Dermoscopy of a skin lesion: 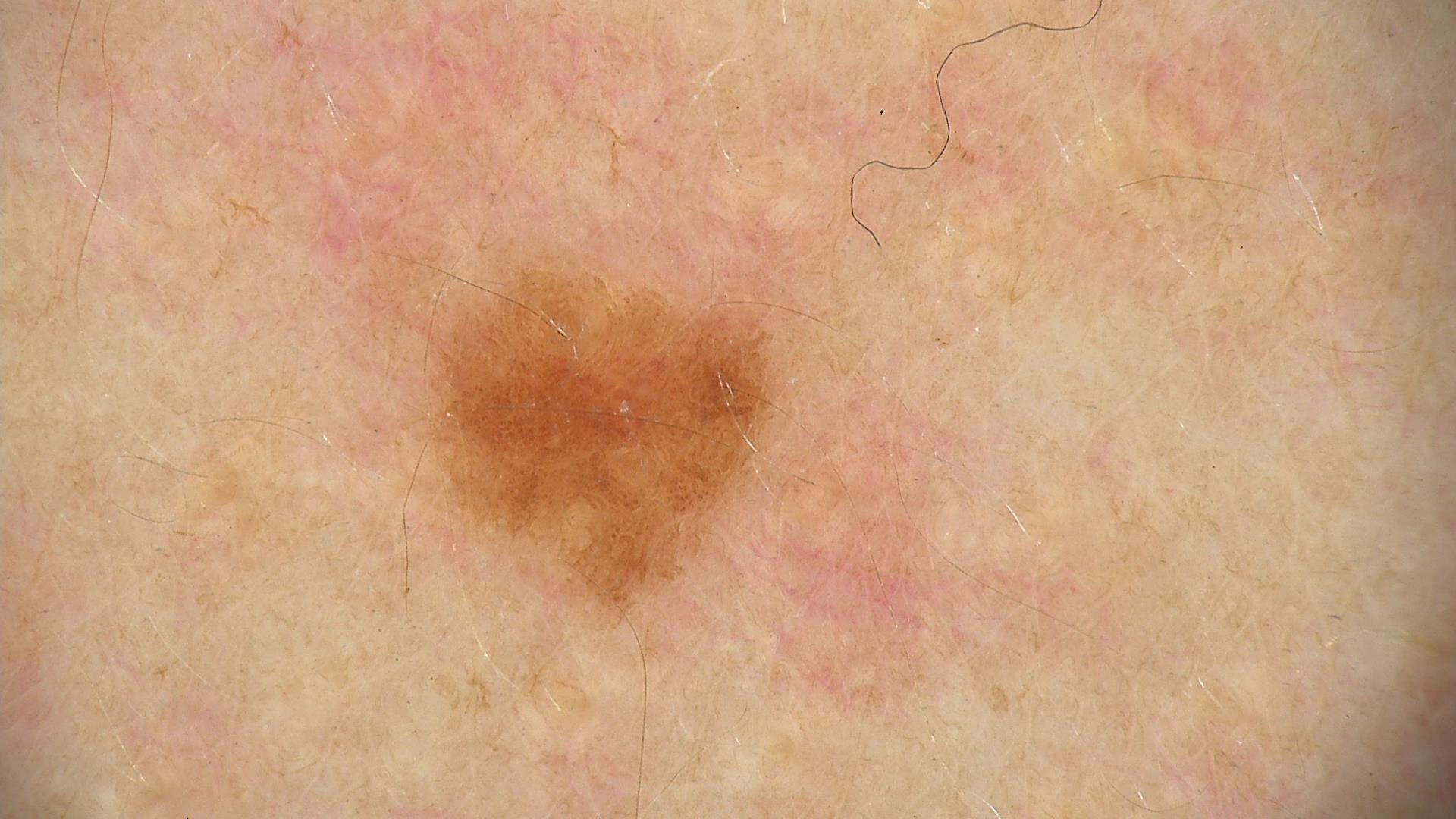Conclusion: Diagnosed as a lentigo simplex.